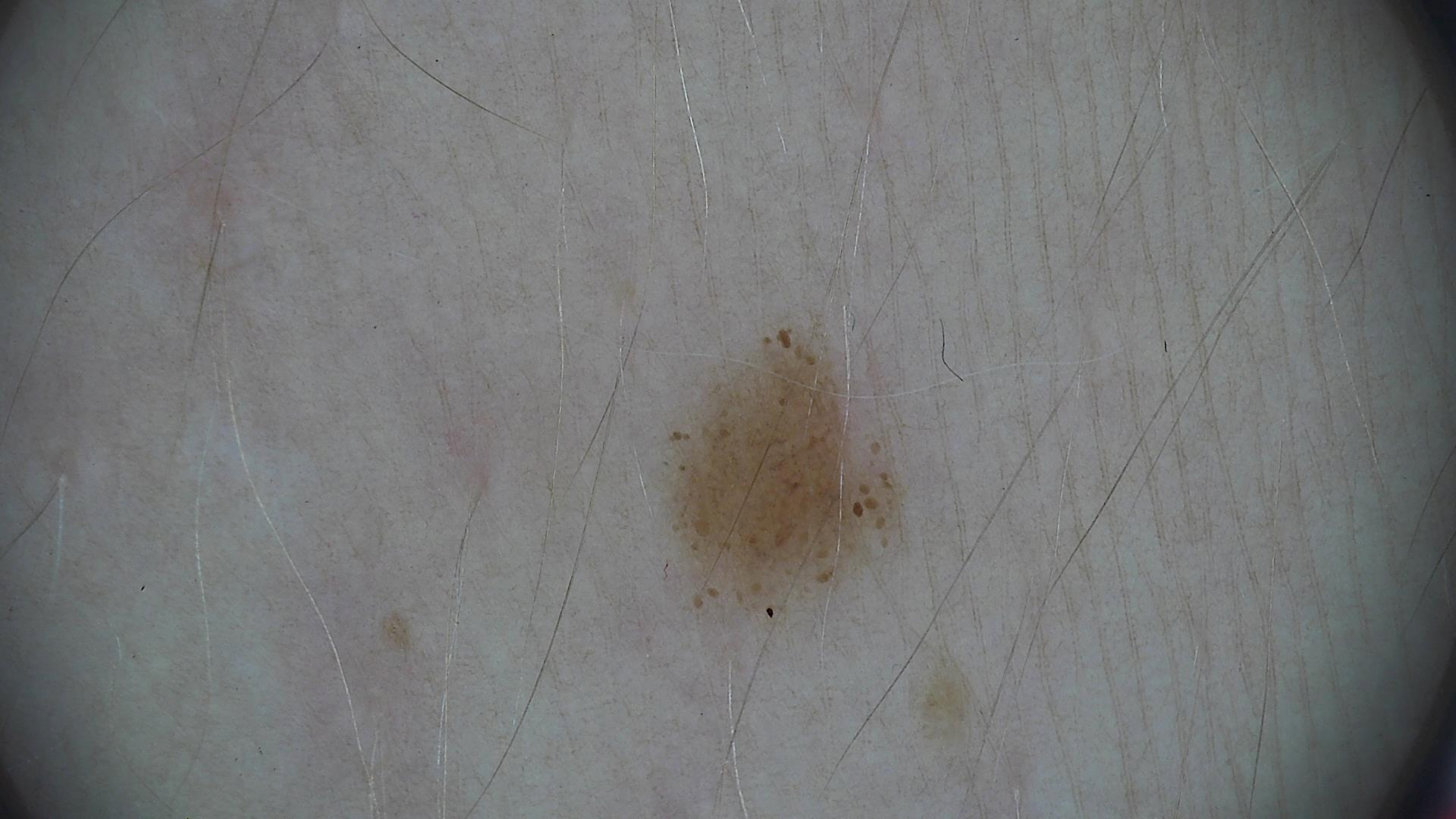A dermoscopic close-up of a skin lesion. Consistent with a dysplastic junctional nevus.